The lesion is described as raised or bumpy; the patient indicates burning and itching; an image taken at a distance; present for about one day; the lesion involves the leg; the patient considered this acne — 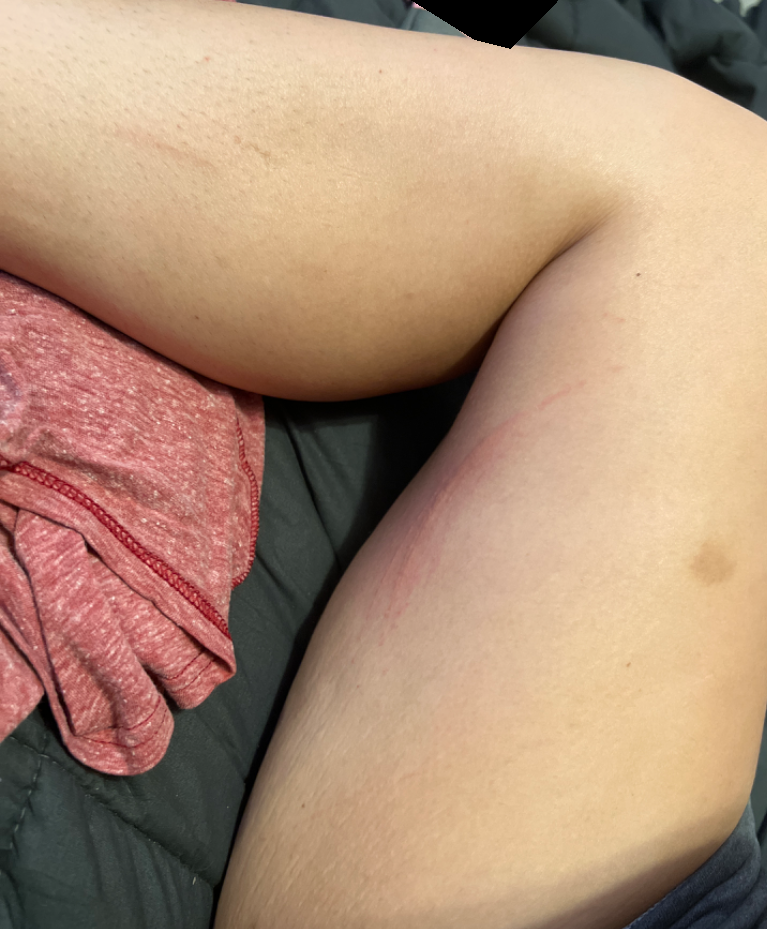• assessment: could not be assessed